A skin lesion imaged with a dermatoscope:
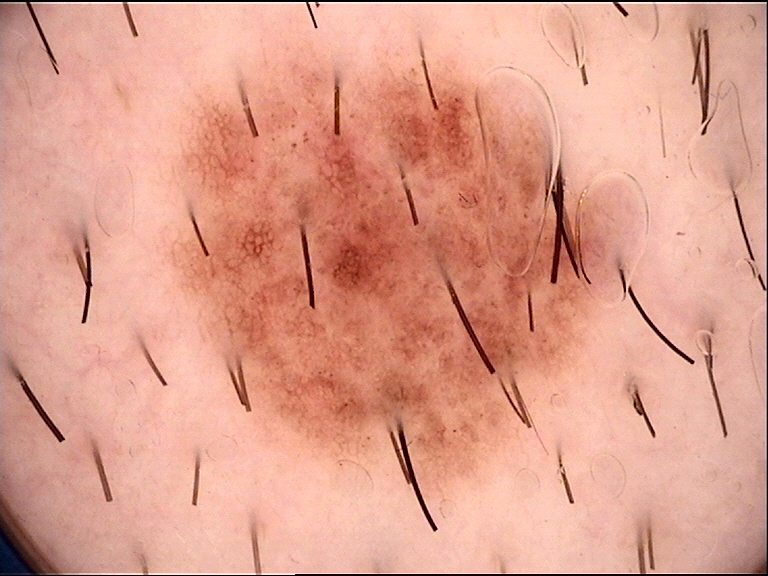assessment: dysplastic compound nevus (expert consensus).